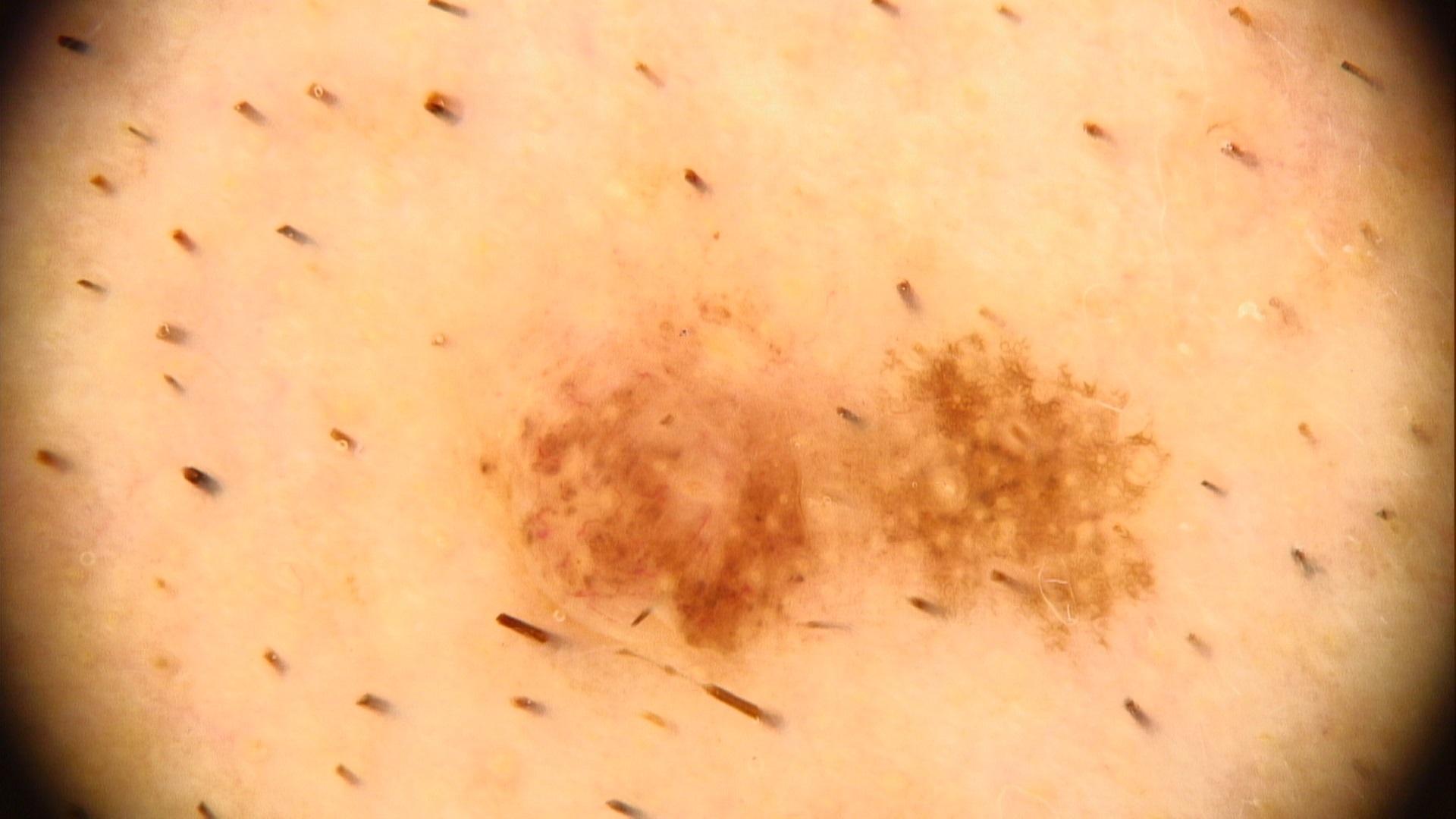  skin_type: III
  image: dermoscopic image
  patient:
    age_approx: 40
    sex: male
  lesion_location:
    region: the head or neck
  diagnosis:
    name: Nevus
    malignancy: benign
    confirmation: expert clinical impression
    lineage: melanocytic